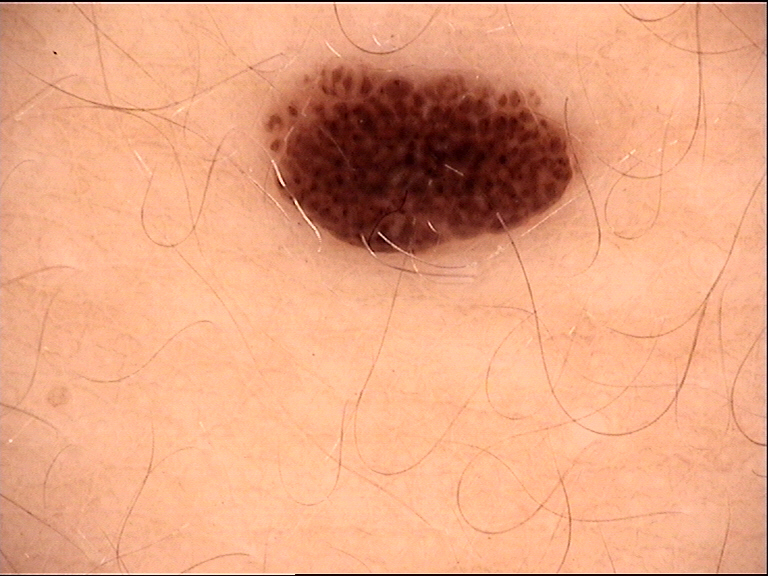Impression: Diagnosed as a compound nevus.